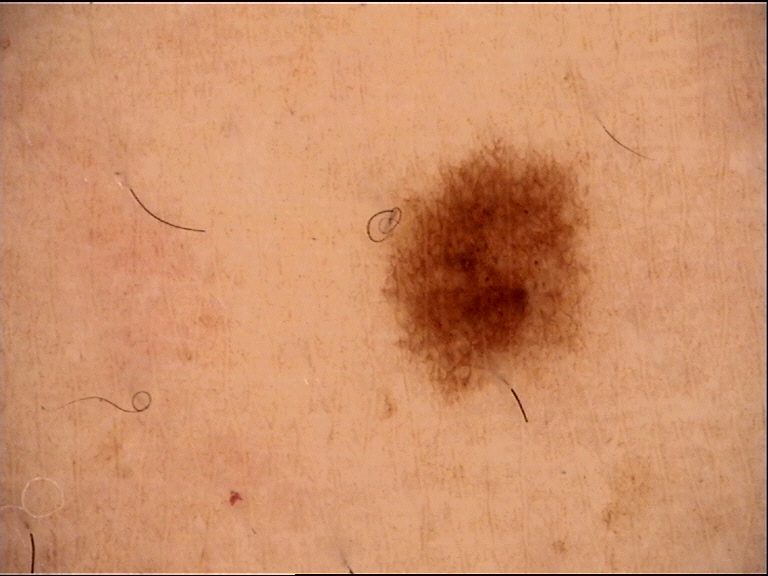Summary:
A skin lesion imaged with a dermatoscope.
Impression:
Consistent with a banal lesion — a junctional nevus.